A dermoscopy image of a skin lesion. A female subject aged 92. Collected as part of a research study, without a referral diagnosis:
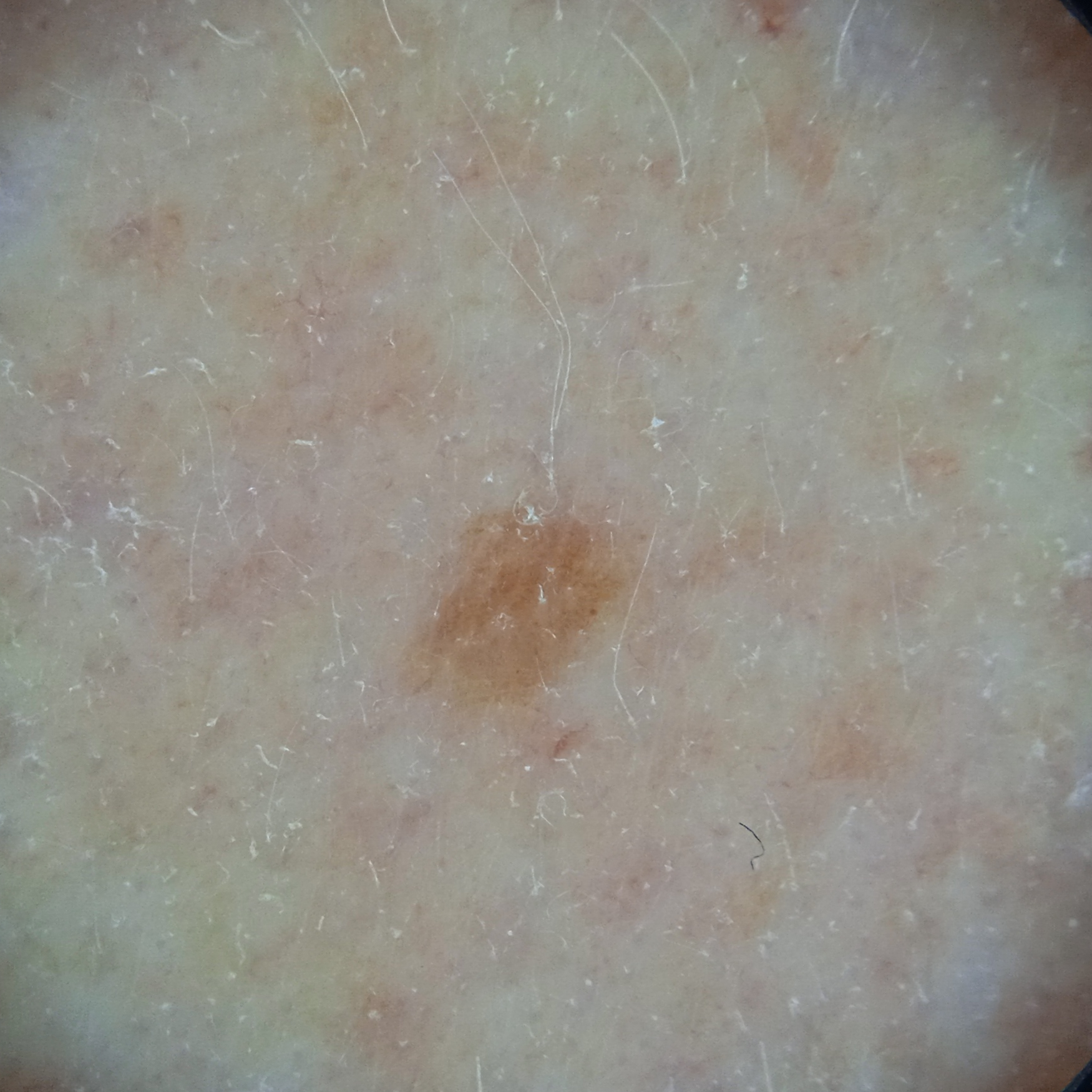The lesion is located on the face. The consensus diagnosis for this lesion was a melanocytic nevus.